A dermoscopy image of a single skin lesion:
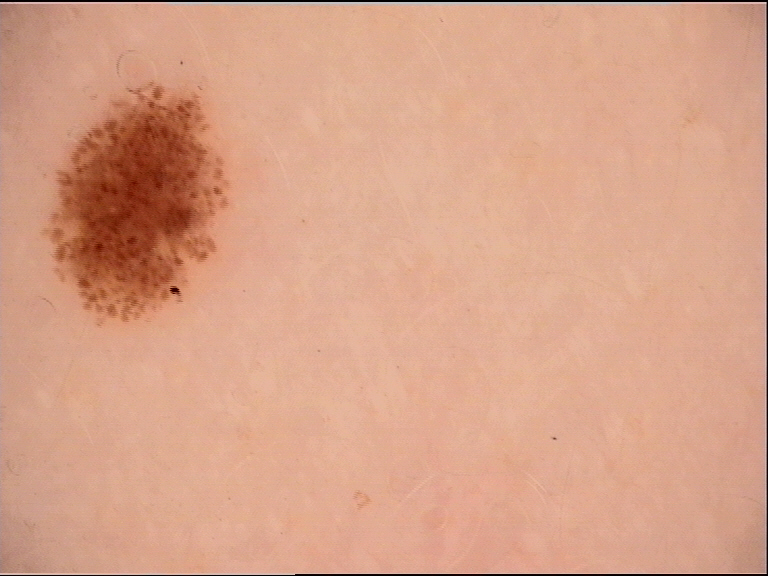This is a banal lesion.
Diagnosed as a junctional nevus.